A dermoscopy image of a single skin lesion.
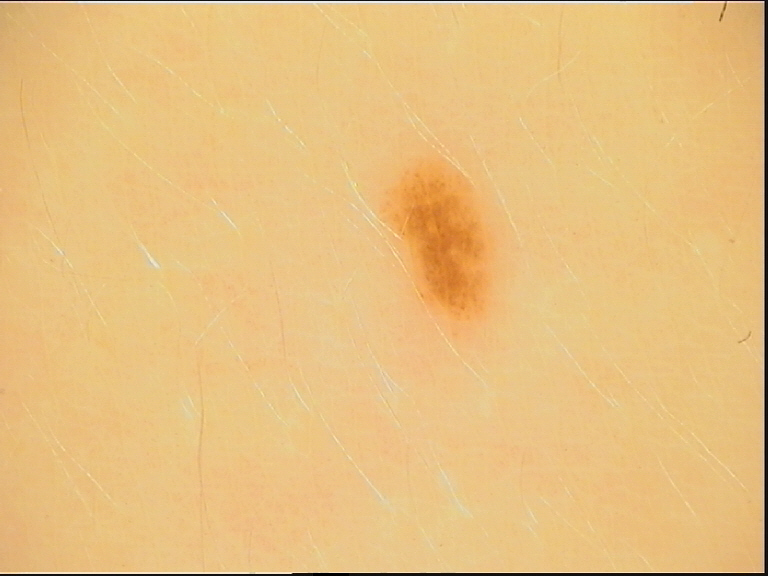Summary: The morphology is that of a banal lesion. Impression: The diagnosis was a junctional nevus.